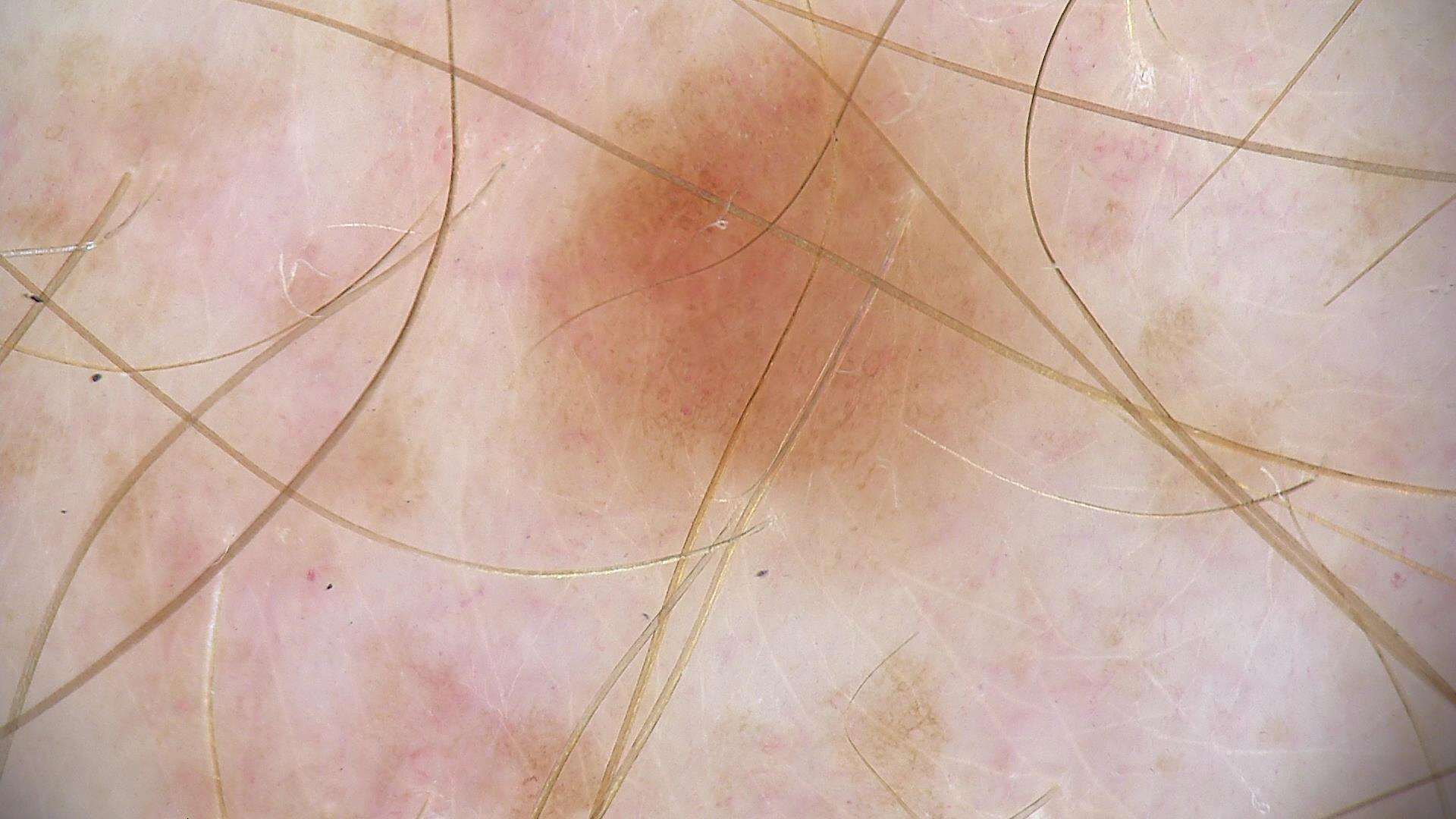assessment = dysplastic junctional nevus (expert consensus).